A dermoscopic view of a skin lesion: 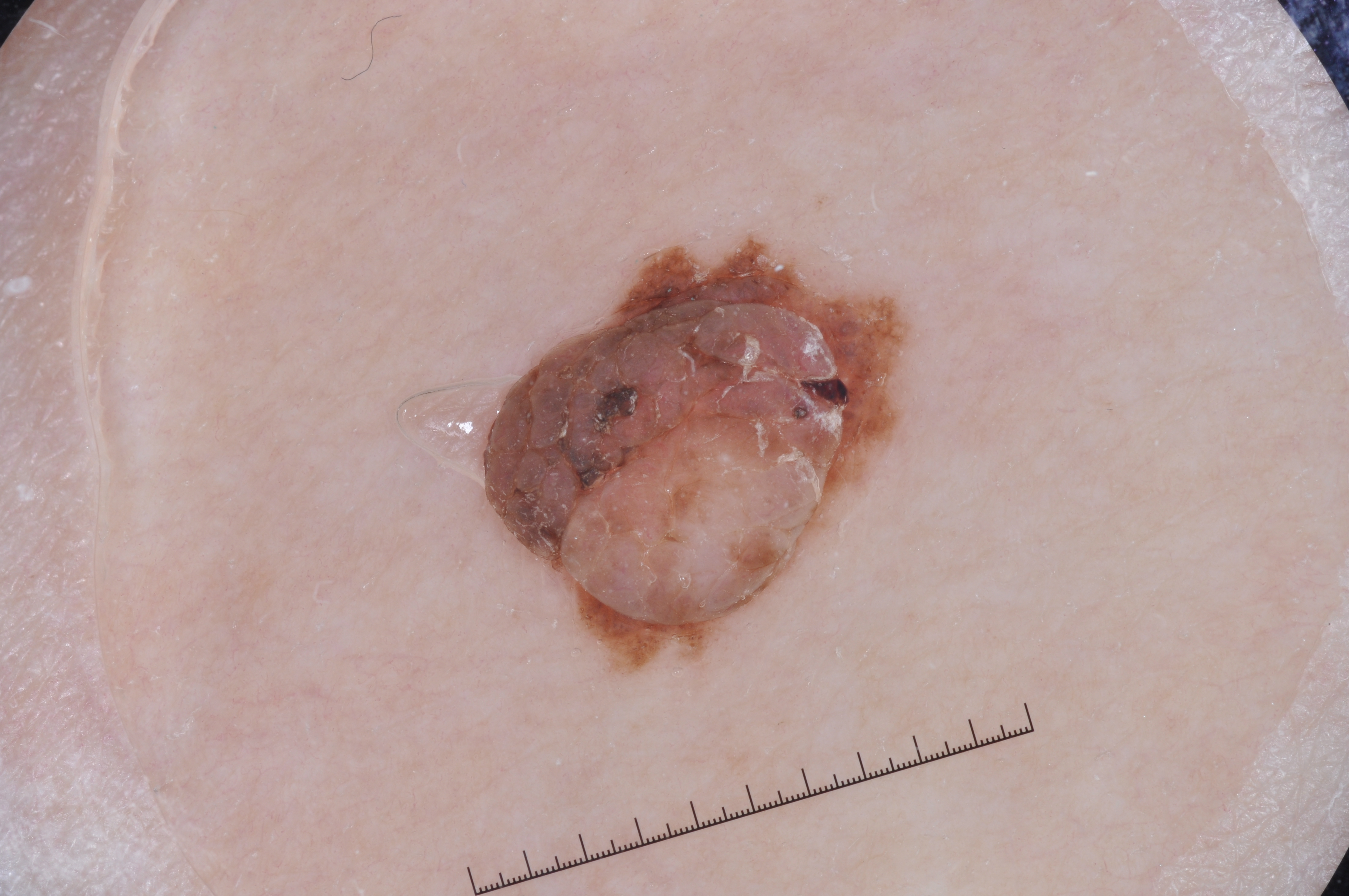  lesion_extent: moderate
  dermoscopic_features:
    present:
      - milia-like cysts
      - pigment network
    absent:
      - streaks
      - negative network
  lesion_location:
    bbox_xyxy:
      - 485
      - 245
      - 906
      - 665
  diagnosis:
    name: melanocytic nevus
    malignancy: benign
    lineage: melanocytic
    provenance: clinical